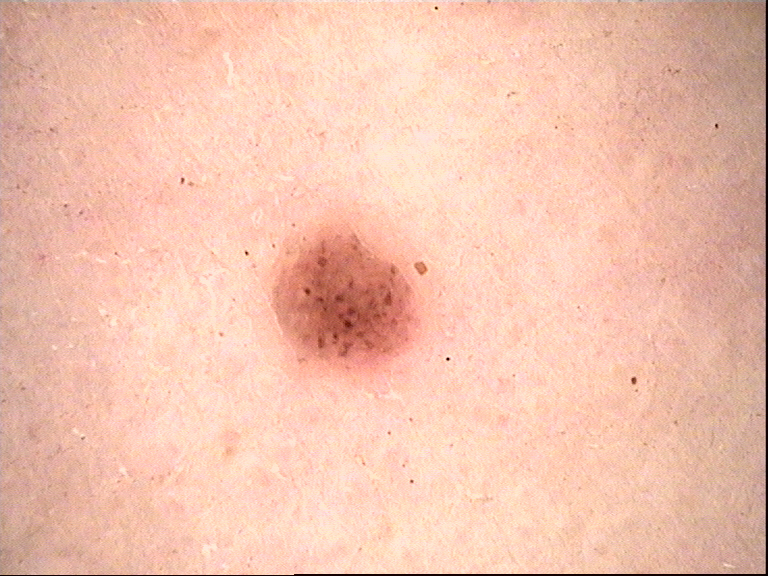modality = dermoscopy, diagnosis = compound nevus (expert consensus).